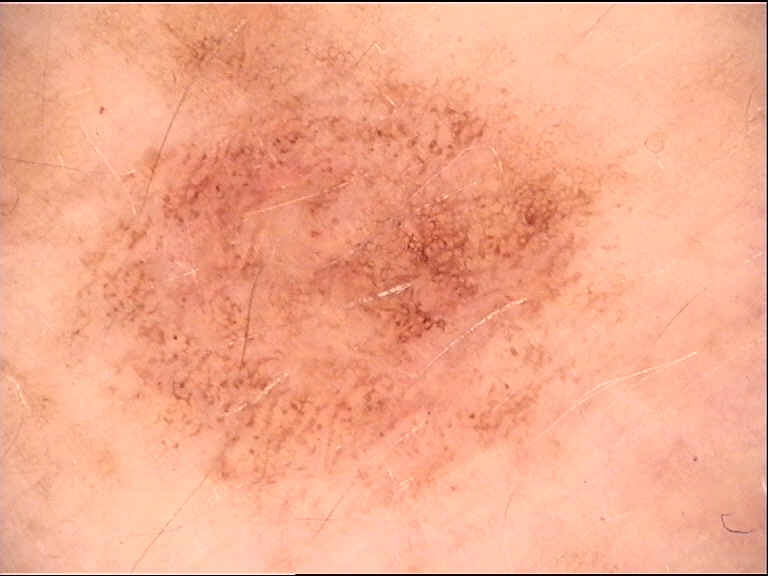{"image": "dermoscopy", "diagnosis": {"name": "dysplastic junctional nevus", "code": "jd", "malignancy": "benign", "super_class": "melanocytic", "confirmation": "expert consensus"}}